Close-up view — 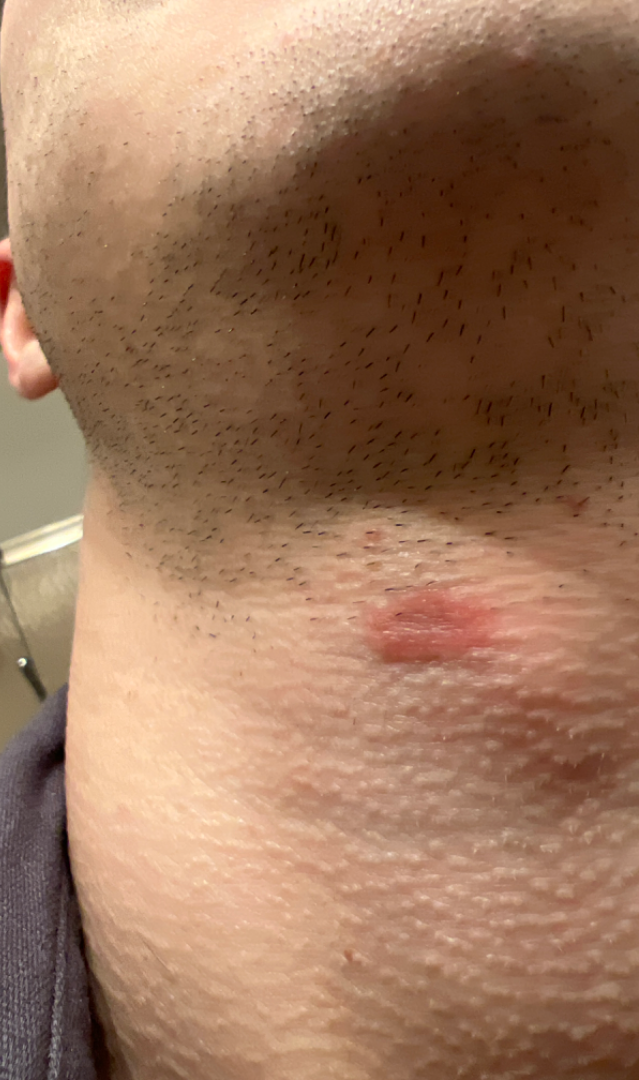{"skin_tone": {"fitzpatrick": "II"}, "differential": {"tied_lead": ["Skin and soft tissue atypical mycobacterial infection", "Basal Cell Carcinoma"], "unlikely": ["Pityriasis rosea"]}}